Located on the leg. The patient reported no systemic symptoms. Reported lesion symptoms include bothersome appearance. This image was taken at an angle. The contributor is female:
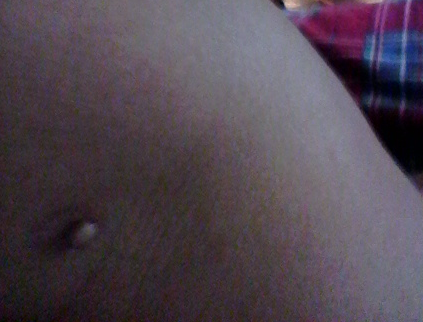Findings:
• assessment · indeterminate